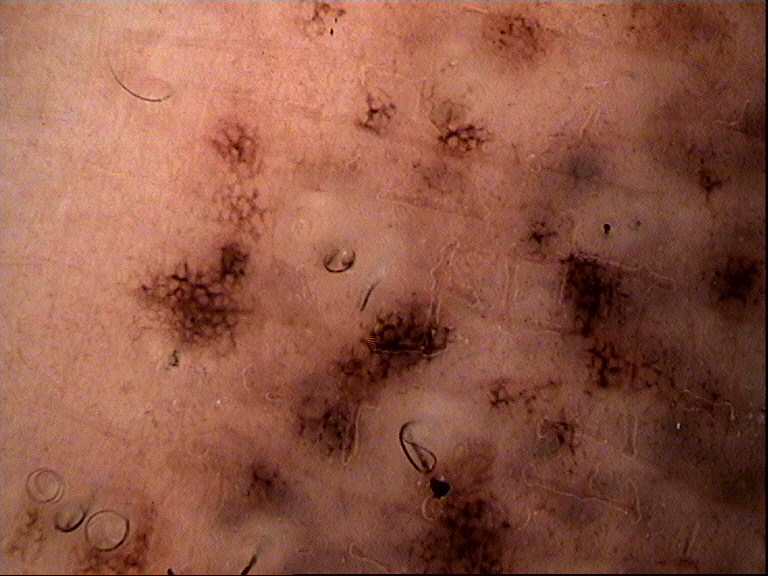A dermoscopic image of a skin lesion. This is a banal lesion. The diagnosis was a congenital compound nevus.